The patient considered this skin that appeared healthy to them. The contributor is 30–39, female. The lesion is described as flat. Reported duration is about one day. No associated lesion symptoms were reported. No constitutional symptoms were reported. This image was taken at an angle — 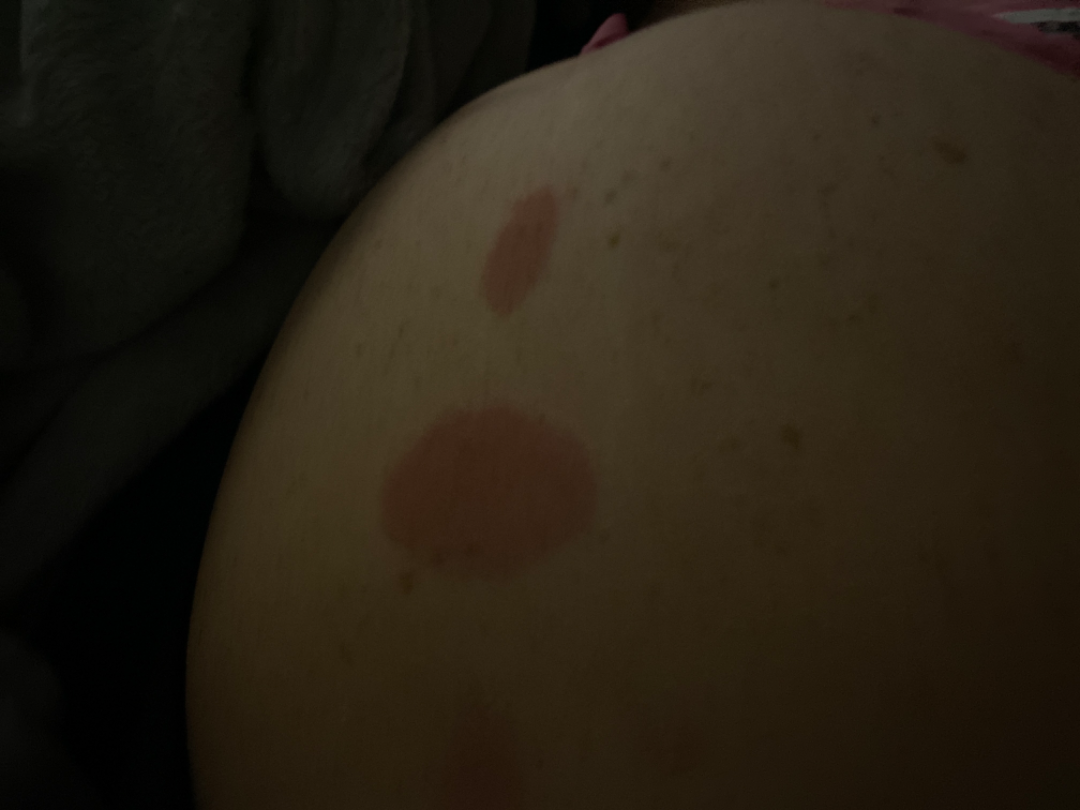The image was not sufficient for the reviewer to characterize the skin condition.